Located on the leg · male subject, age 18–29 · a close-up photograph — 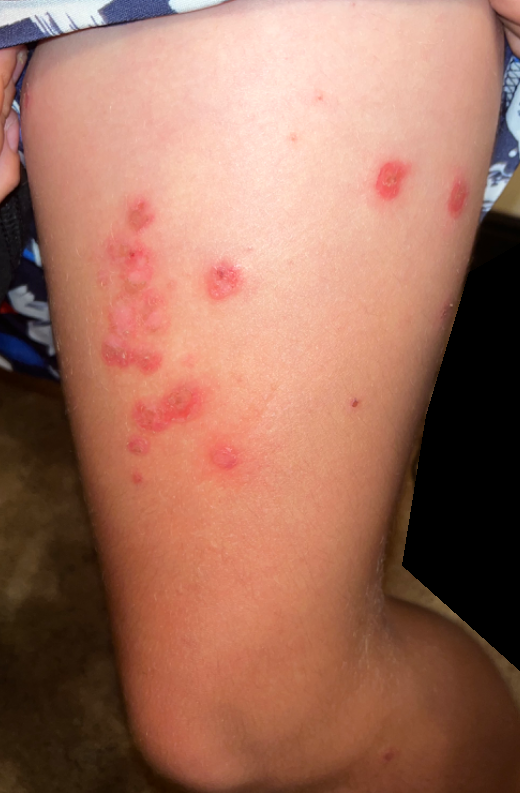Findings: Impetigo and Bullous dermatitis, NOS were considered with similar weight.